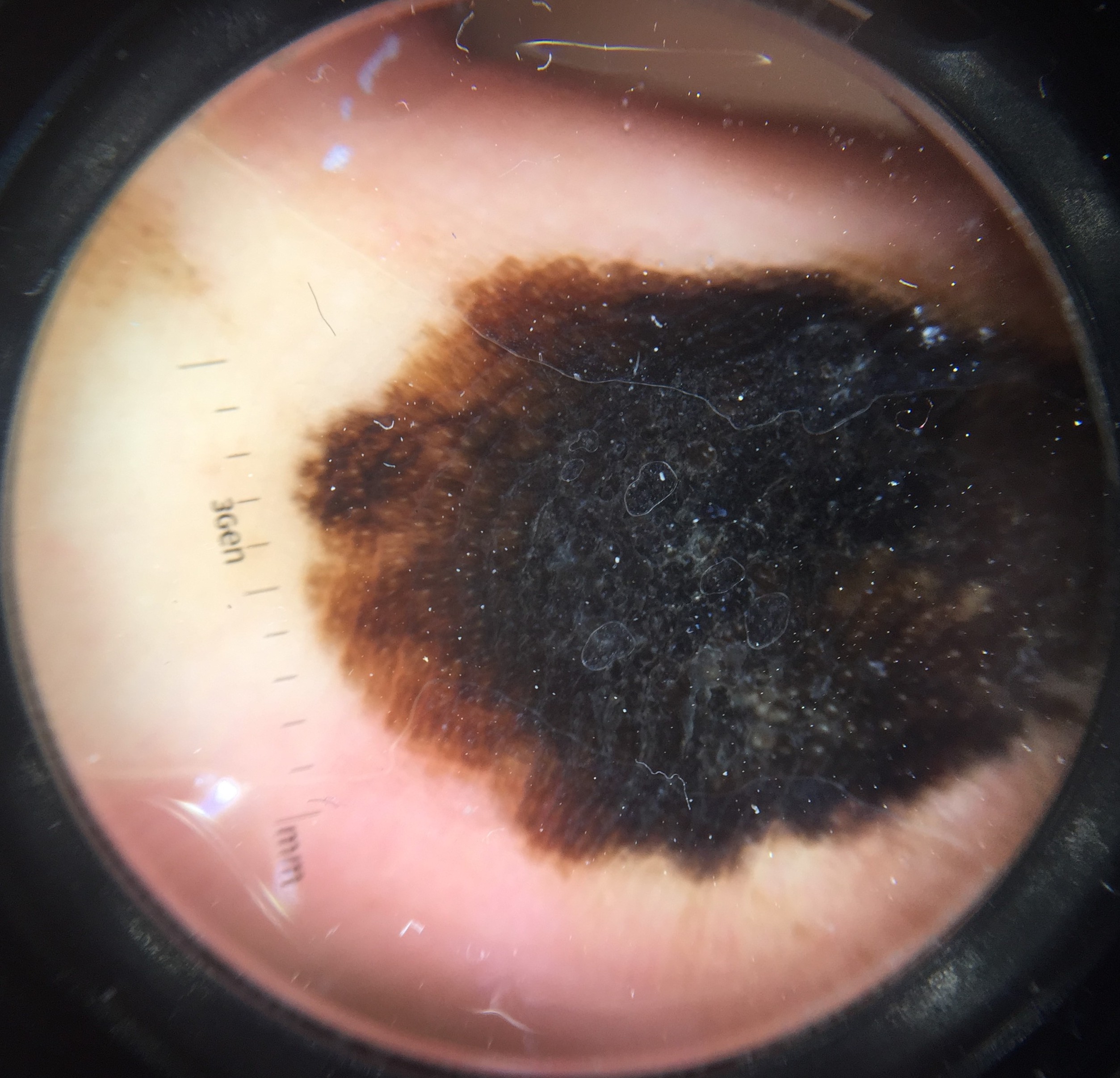Findings:
• label: acral lentiginous melanoma (biopsy-proven)